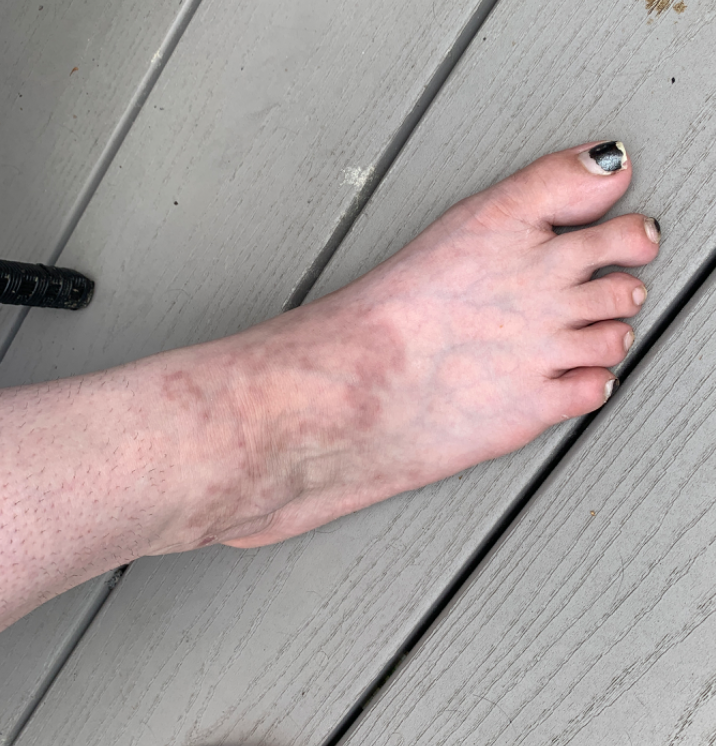{
  "symptoms": [
    "darkening",
    "enlargement",
    "bothersome appearance"
  ],
  "patient": "female, age 18–29",
  "patient_category": "skin that appeared healthy to them",
  "duration": "more than one year",
  "shot_type": "at a distance",
  "differential": {
    "tied_lead": [
      "Granuloma annulare",
      "Livedo reticularis",
      "Contact dermatitis"
    ],
    "unlikely": [
      "Stasis Dermatitis"
    ]
  }
}